Fitzpatrick II; a clinical close-up photograph of a skin lesion; a male patient in their 50s: 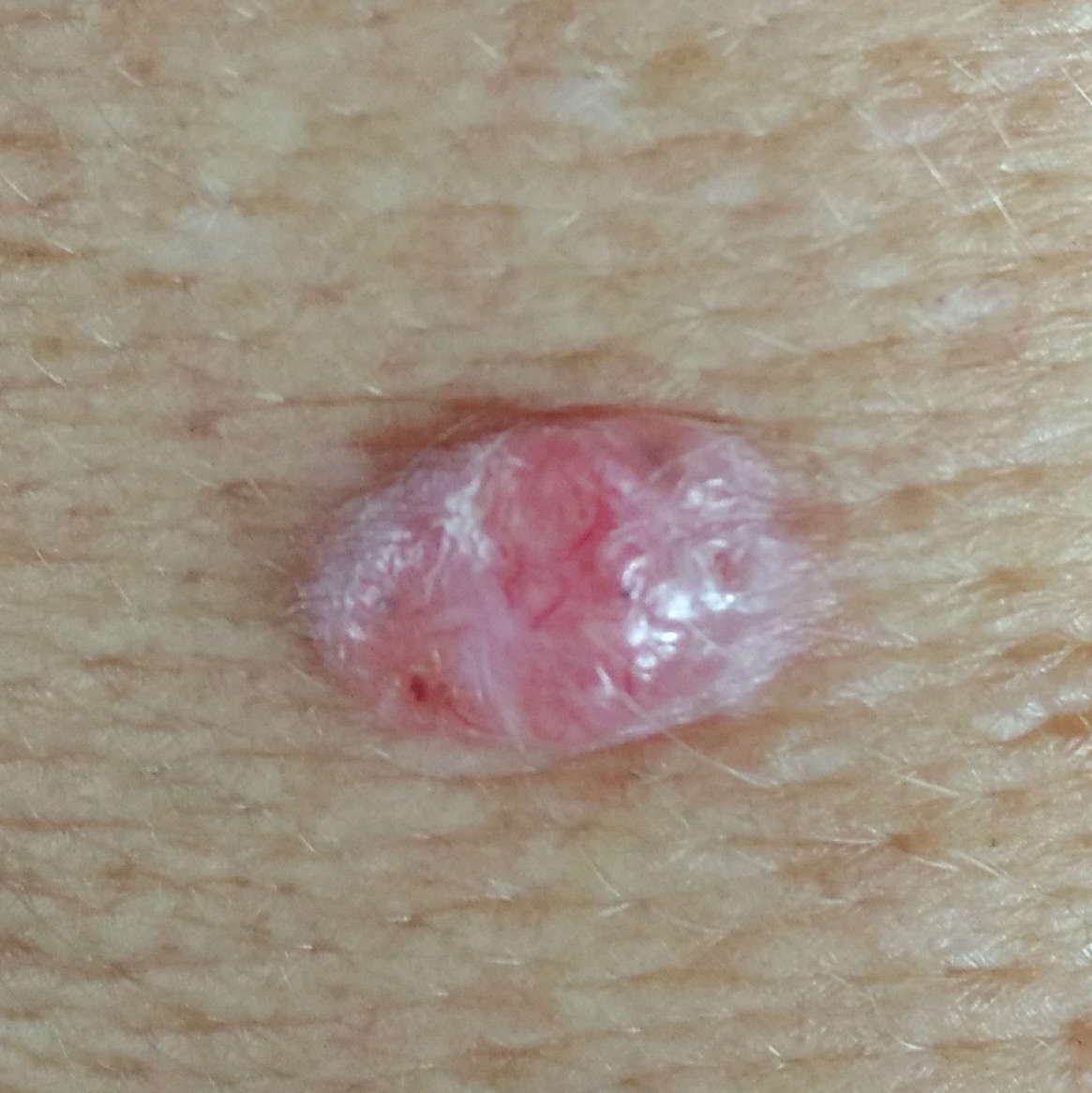diagnosis = basal cell carcinoma (biopsy-proven)